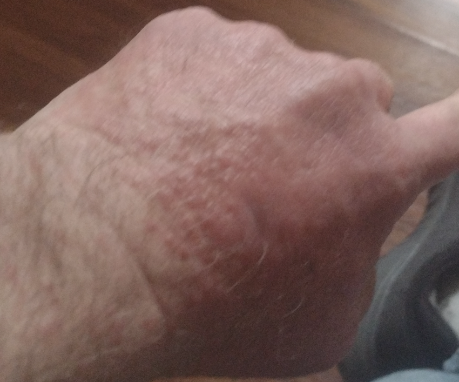Findings:
The reviewer was unable to grade this case for skin condition.